The photo was captured at an angle · the back of the hand is involved: 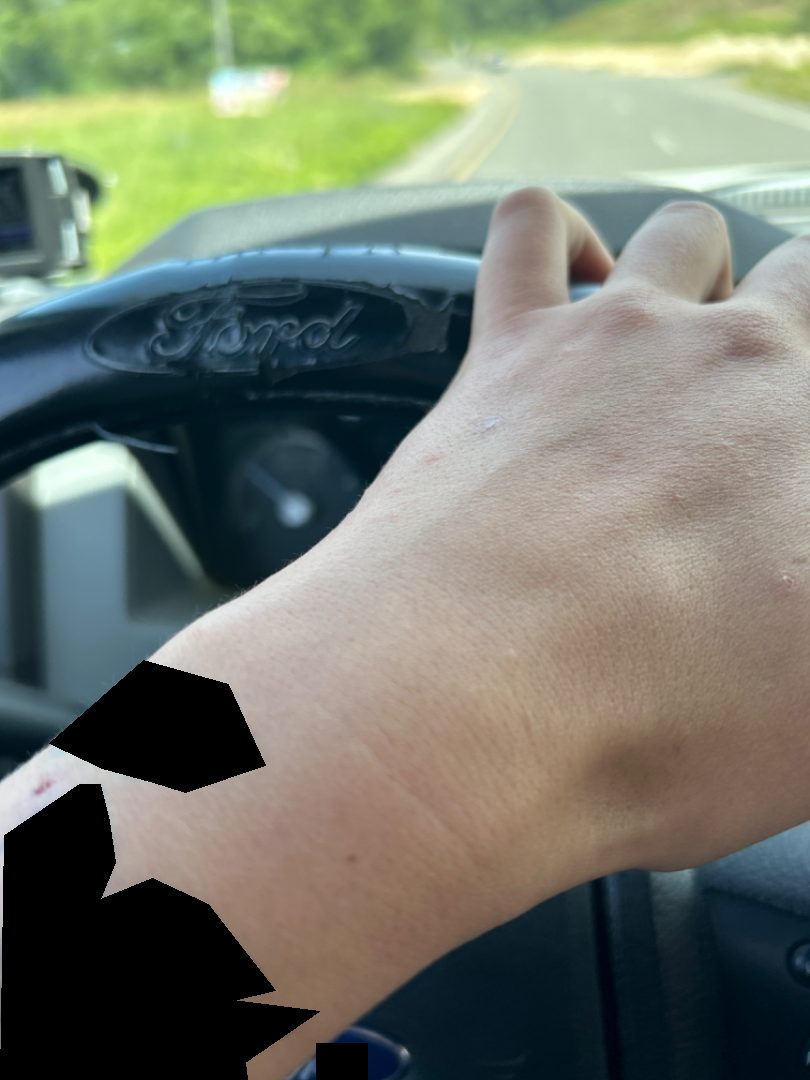Impression: Diagnostic features were not clearly distinguishable in this photograph. History: Symptoms reported: itching, burning and enlargement. The patient considered this a rash. Reported duration is less than one week. Texture is reported as raised or bumpy. No associated systemic symptoms reported.